Few moles overall by the patient's own estimate · by self-report, no prior organ transplant and no immunosuppression · collected as part of a research study, without a referral diagnosis · a skin lesion imaged with a dermatoscope — 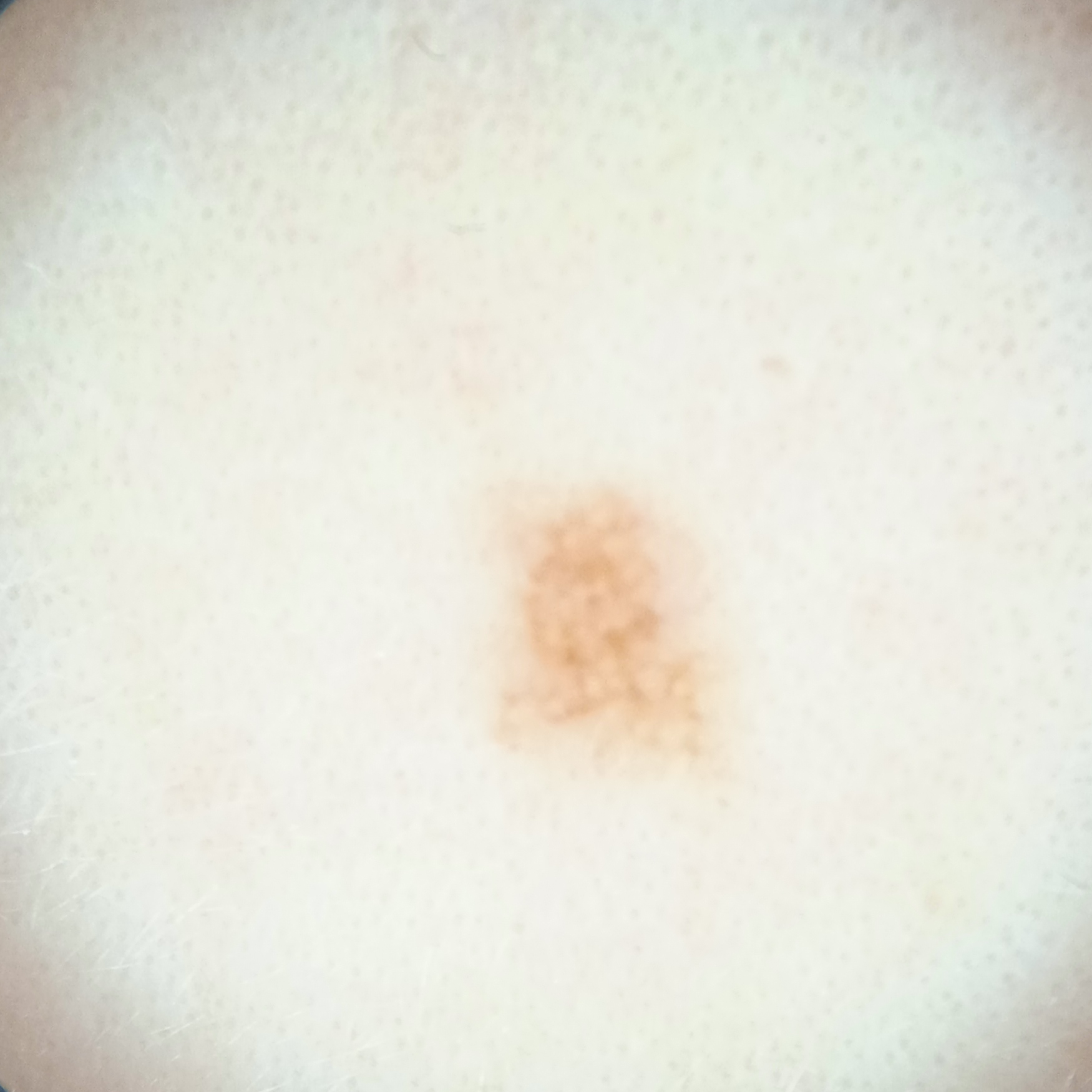The lesion is on the face. The lesion is about 3.2 mm across. Dermatologist review favored a melanocytic nevus.